The affected area is the back of the torso, front of the torso, leg, head or neck and arm · an image taken at a distance — 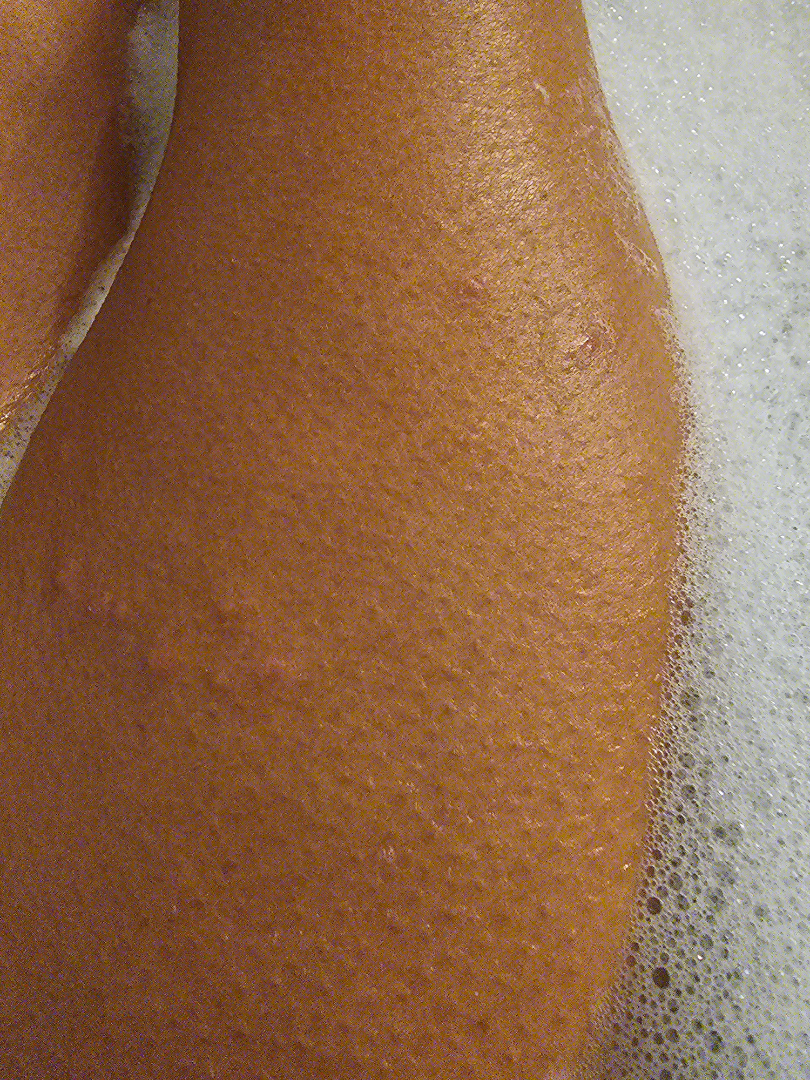Clinical context:
The lesion is associated with burning and itching. The patient indicates the lesion is raised or bumpy. Fitzpatrick IV; lay reviewers estimated Monk skin tone scale 6 (US pool) or 5 (India pool). The condition has been present for less than one week. The patient considered this skin that appeared healthy to them.
Assessment:
On remote dermatologist review: Verruca vulgaris (weight 0.54); SK/ISK (weight 0.23); Molluscum Contagiosum (weight 0.23).